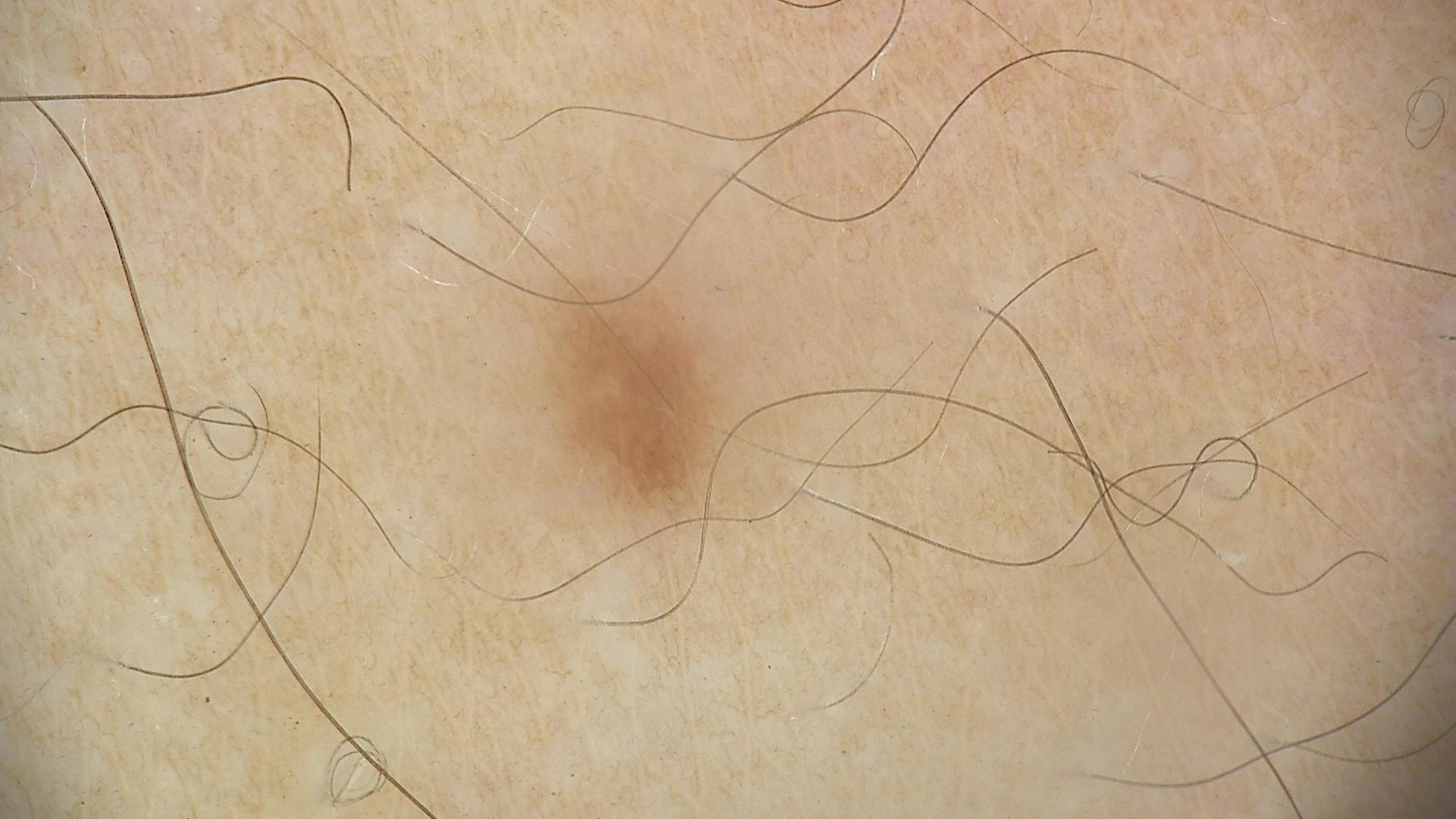  image: dermoscopy
  diagnosis:
    name: dysplastic junctional nevus
    code: jd
    malignancy: benign
    super_class: melanocytic
    confirmation: expert consensus